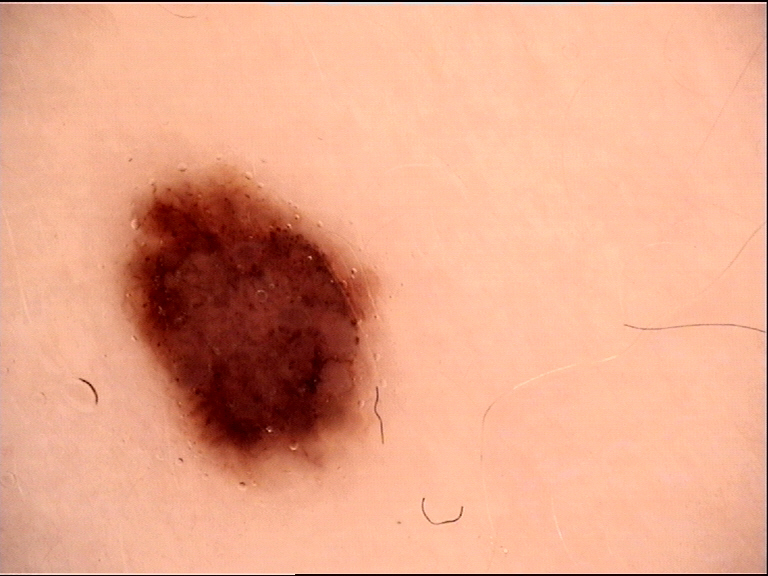A skin lesion imaged with a dermatoscope.
The architecture is that of a banal lesion.
Diagnosed as a compound nevus.